A skin lesion imaged with a dermatoscope.
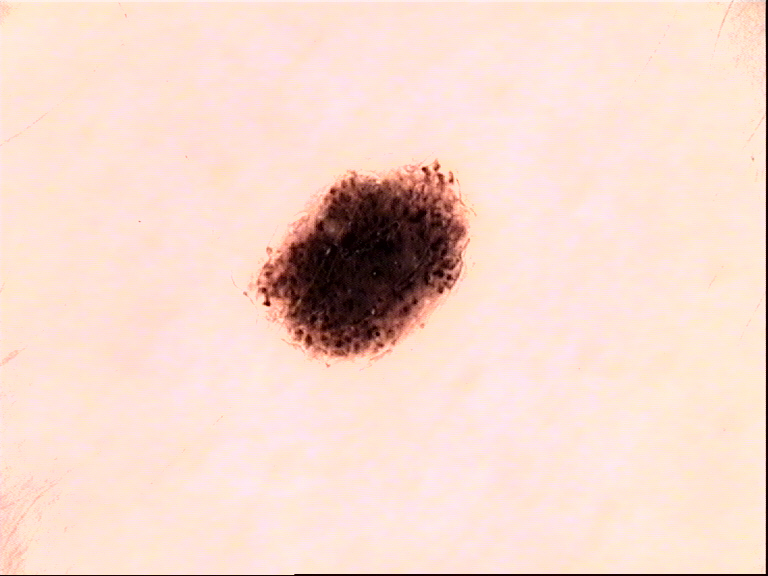The diagnosis was a benign lesion — a dysplastic compound nevus.